An image taken at a distance; the arm is involved; Fitzpatrick III; the lesion is described as flat; the condition has been present for less than one week; female subject, age 60–69; the lesion is associated with bothersome appearance.
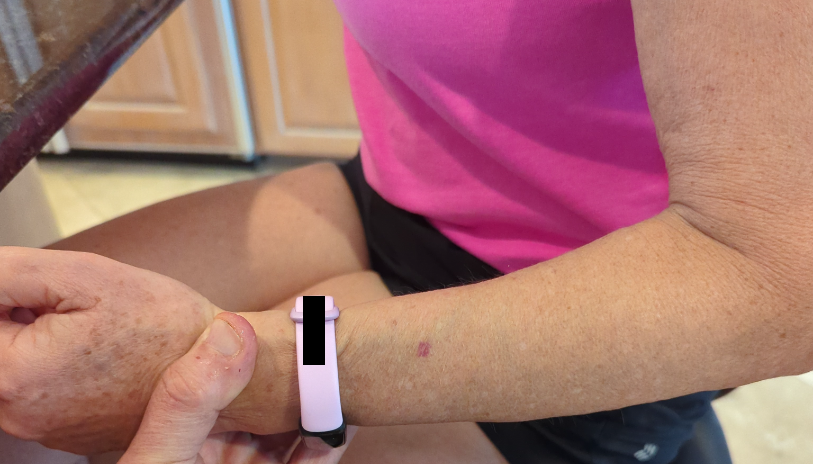The skin condition could not be confidently assessed from this image.